A skin lesion imaged with a dermatoscope.
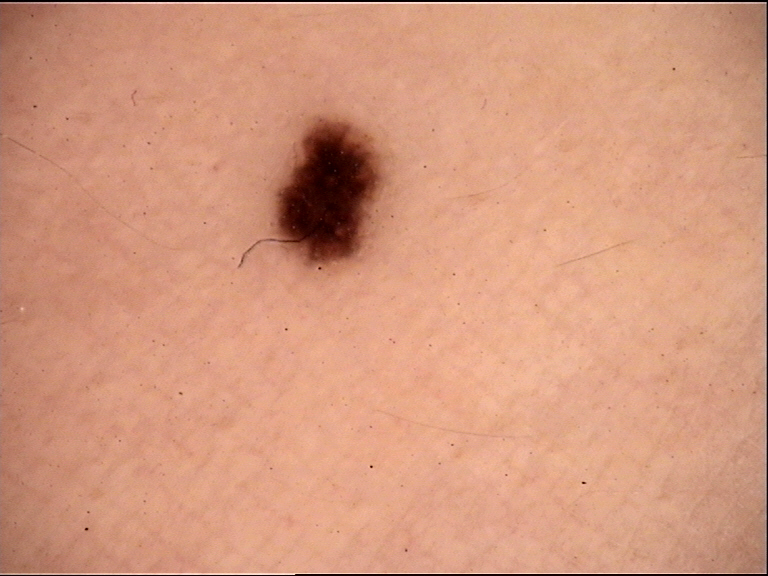  diagnosis:
    name: dysplastic junctional nevus
    code: jd
    malignancy: benign
    super_class: melanocytic
    confirmation: expert consensus